The lesion involves the leg; an image taken at an angle; texture is reported as raised or bumpy; present for less than one week; the contributor is a male aged 40–49 — 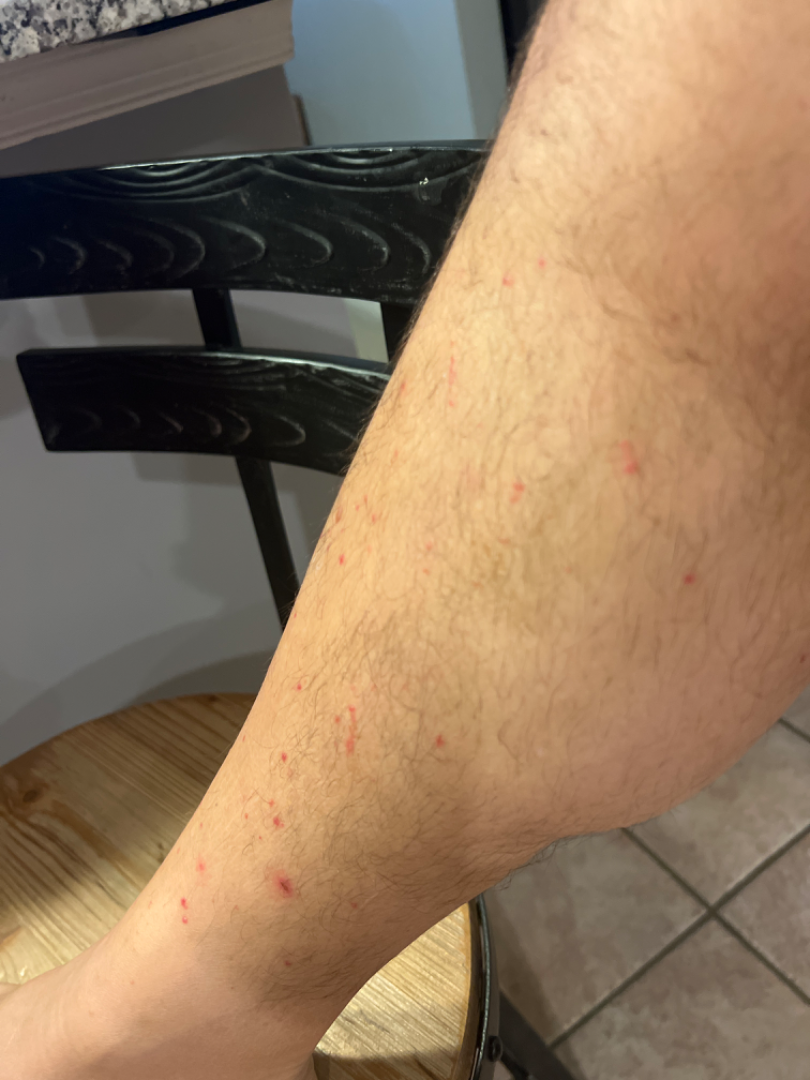<report>
<differential>
  <leading>Leukocytoclastic Vasculitis</leading>
  <unlikely>Drug Rash, Scabies, Insect Bite, Pigmented purpuric eruption</unlikely>
</differential>
</report>